A skin lesion imaged with a dermatoscope · a female patient about 35 years old:
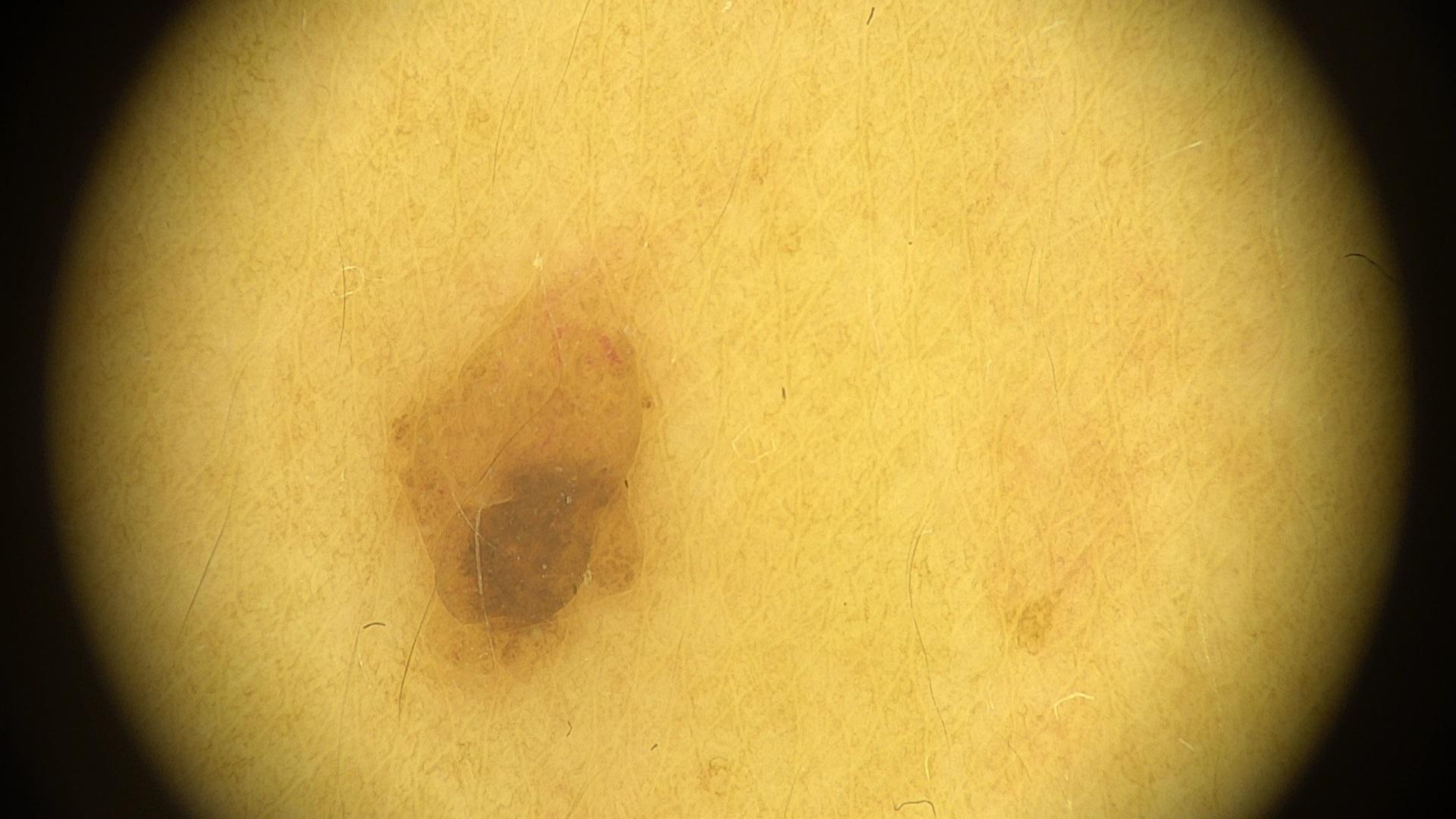Located on the trunk.
Consistent with a nevus.